A dermoscopic image of a skin lesion: 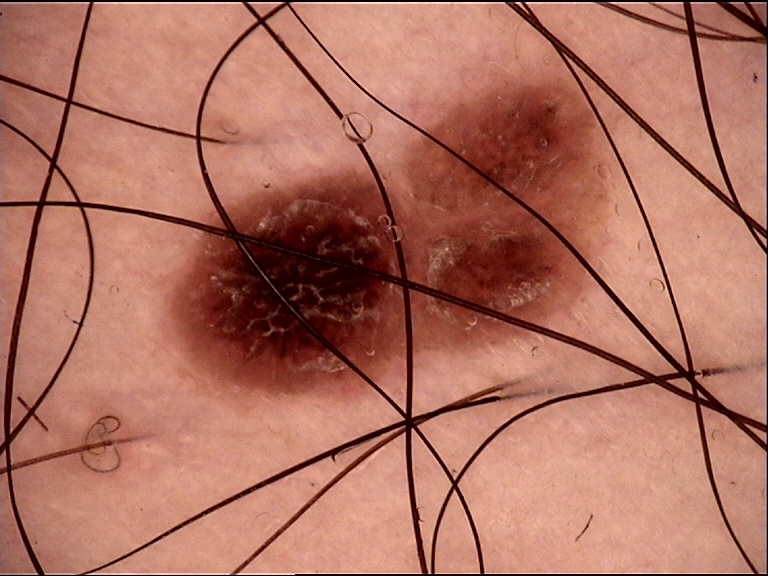{
  "diagnosis": {
    "name": "dysplastic compound nevus",
    "code": "cd",
    "malignancy": "benign",
    "super_class": "melanocytic",
    "confirmation": "expert consensus"
  }
}